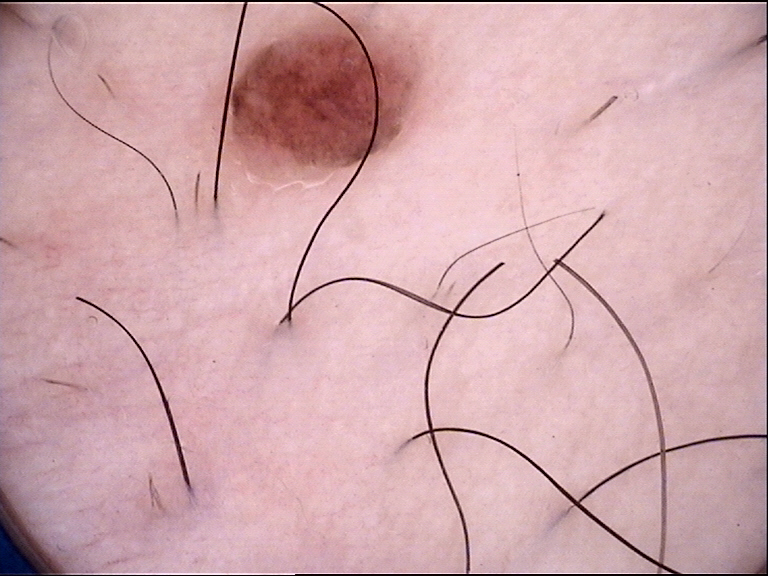image type — dermoscopy | classification — banal | diagnostic label — compound nevus (expert consensus).